Skin tone: Fitzpatrick phototype IV · reported lesion symptoms include pain and itching · close-up view — 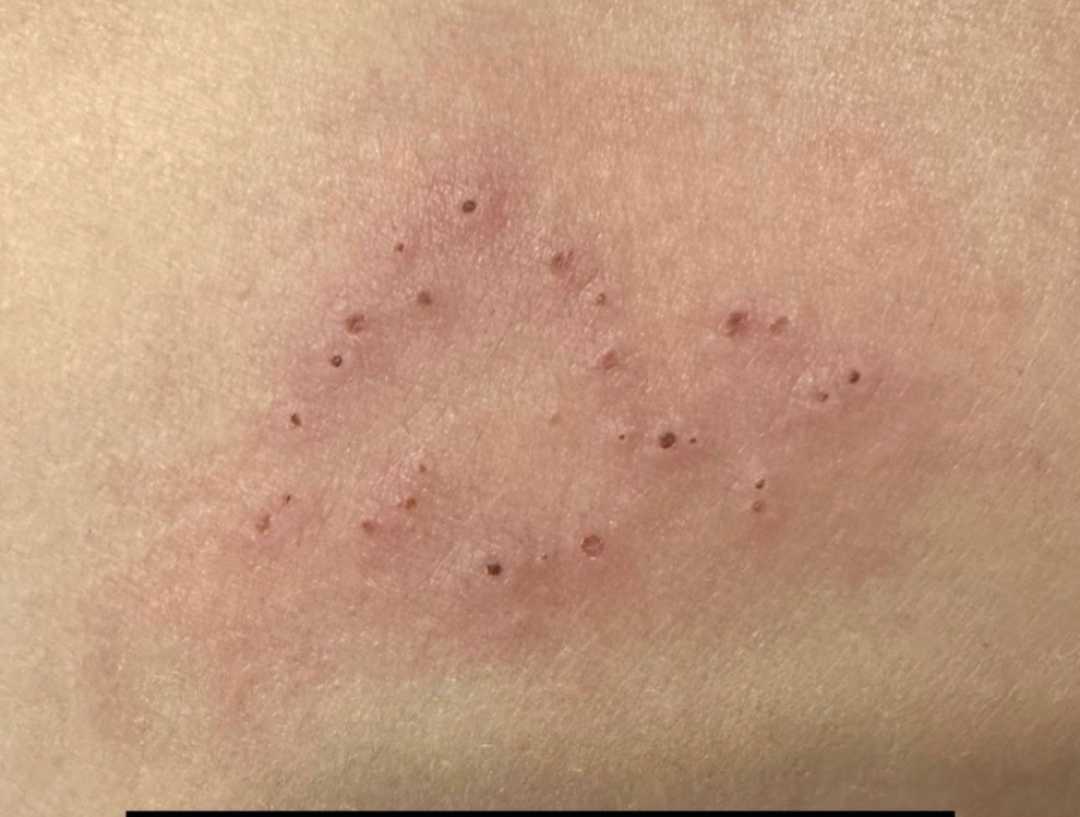  differential:
    leading:
      - Herpes Zoster
    considered:
      - Herpes Simplex